Dermoscopy of a skin lesion.
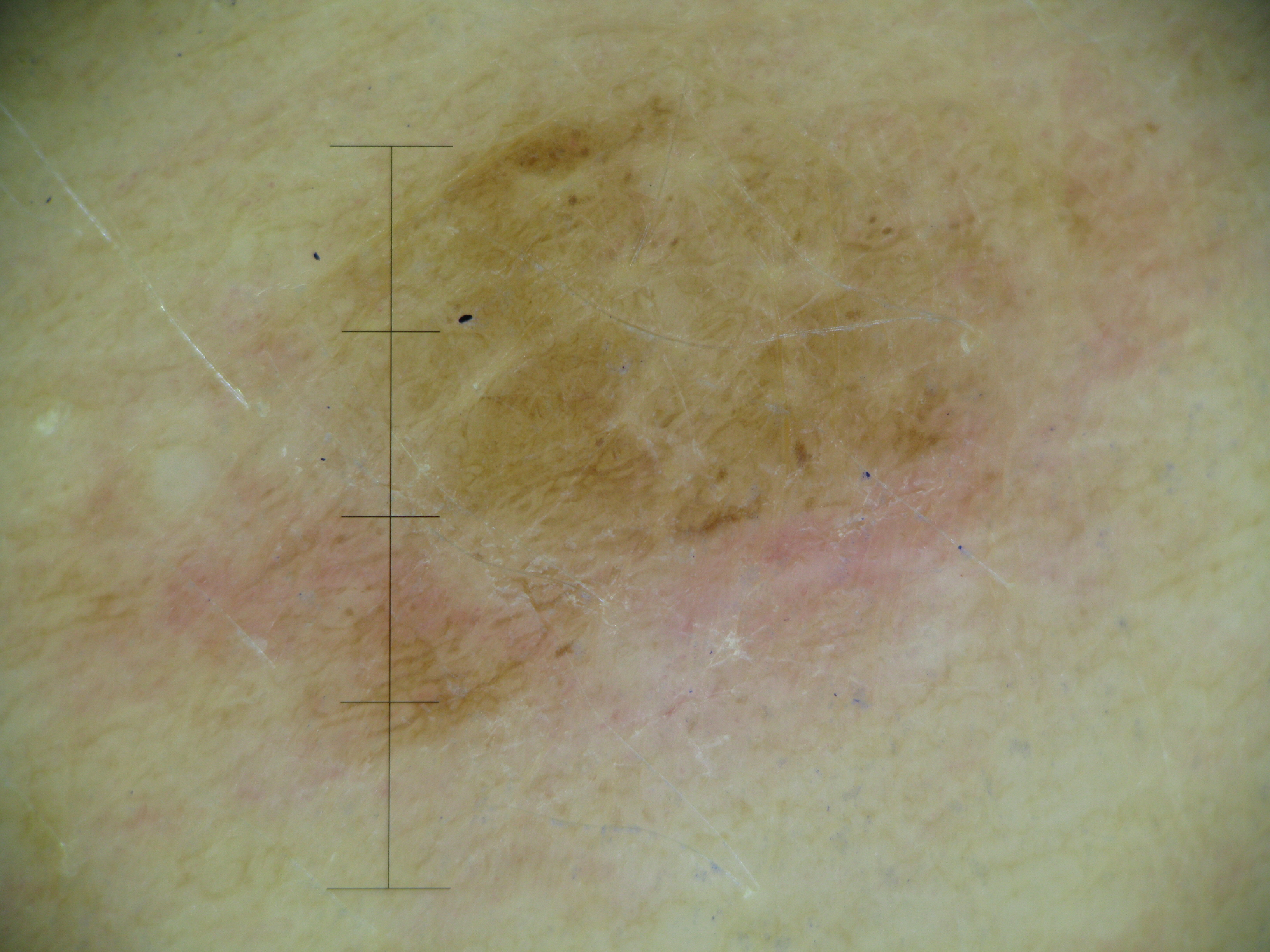assessment=compound nevus (expert consensus).